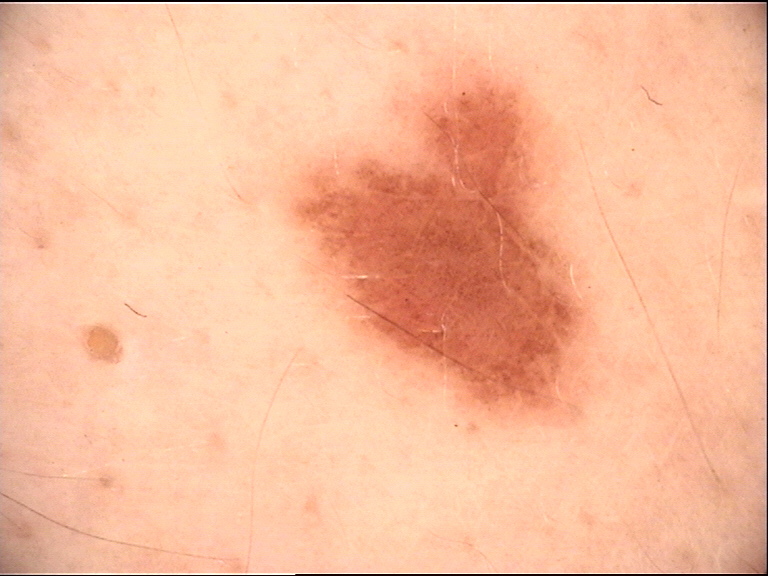Conclusion: Labeled as a dysplastic junctional nevus.